Symptoms reported: itching and burning · the lesion is described as fluid-filled · the lesion involves the back of the hand · the condition has been present for about one day · the patient is 50–59, female · a close-up photograph · the patient considered this a rash:
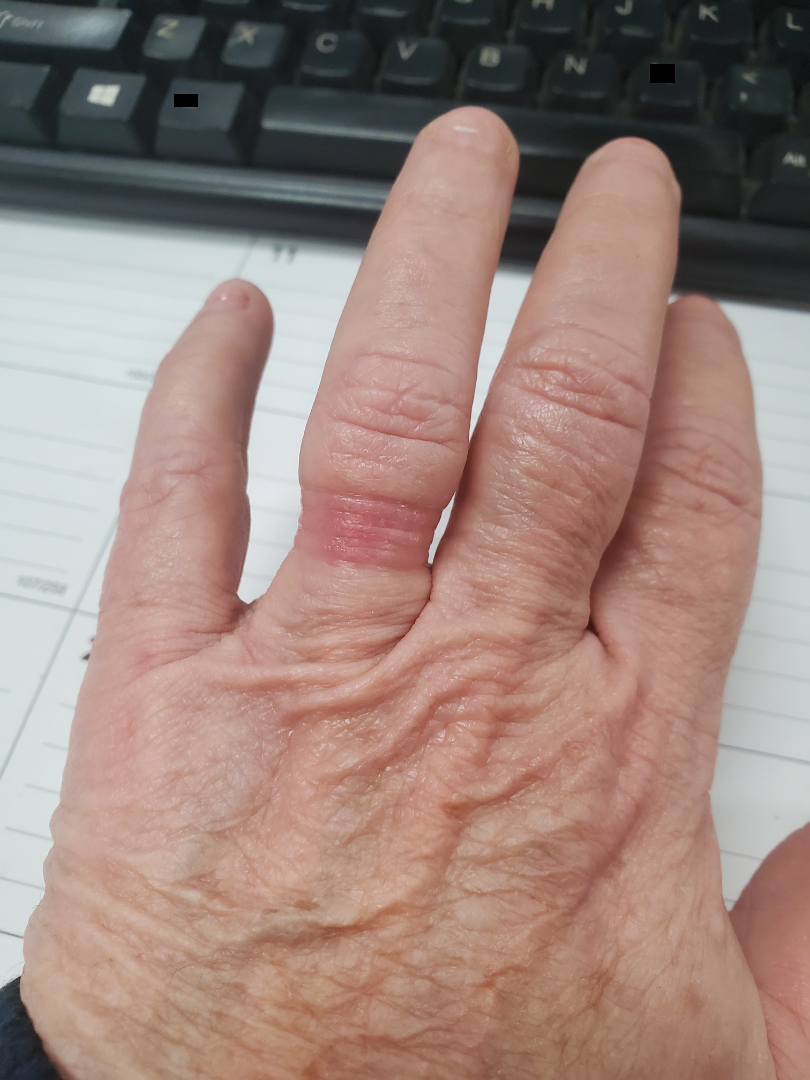impression — one reviewing dermatologist: most consistent with Irritant Contact Dermatitis; also consider Allergic Contact Dermatitis.